A dermoscopic photograph of a skin lesion:
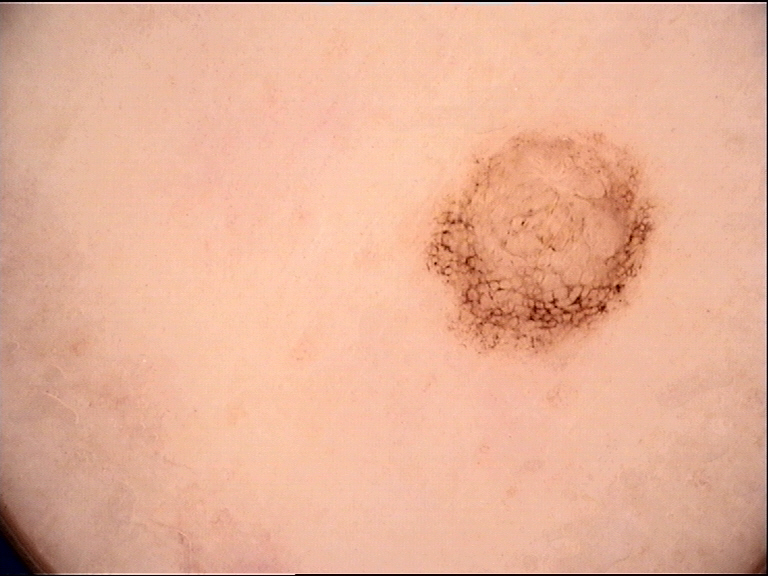• label: dysplastic compound nevus (expert consensus)